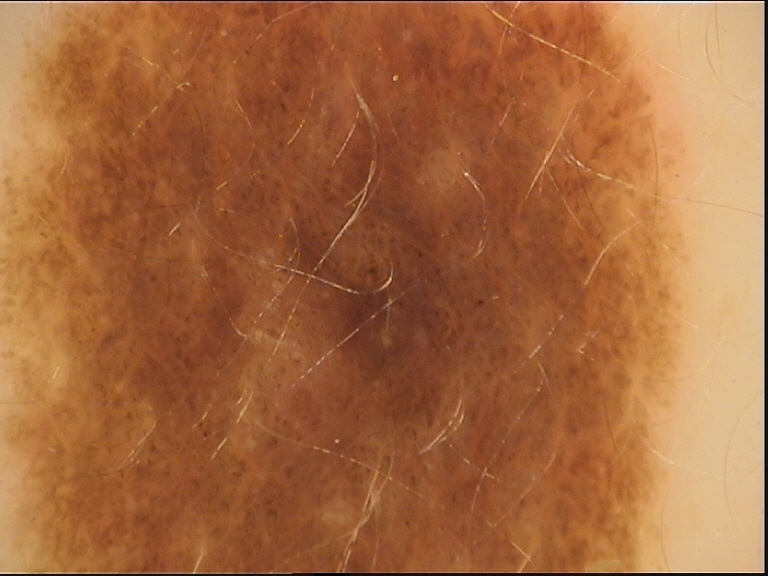Dermoscopy of a skin lesion. The diagnosis was a dysplastic compound nevus.